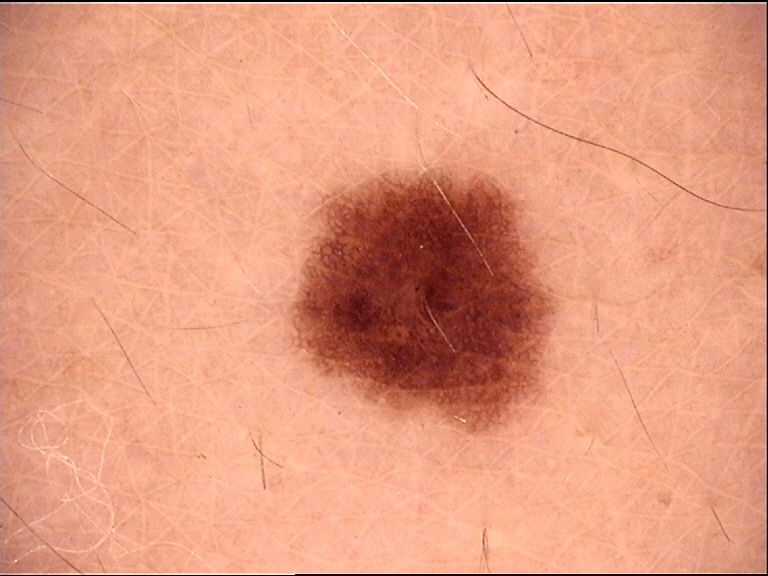Labeled as a benign lesion — a dysplastic junctional nevus.